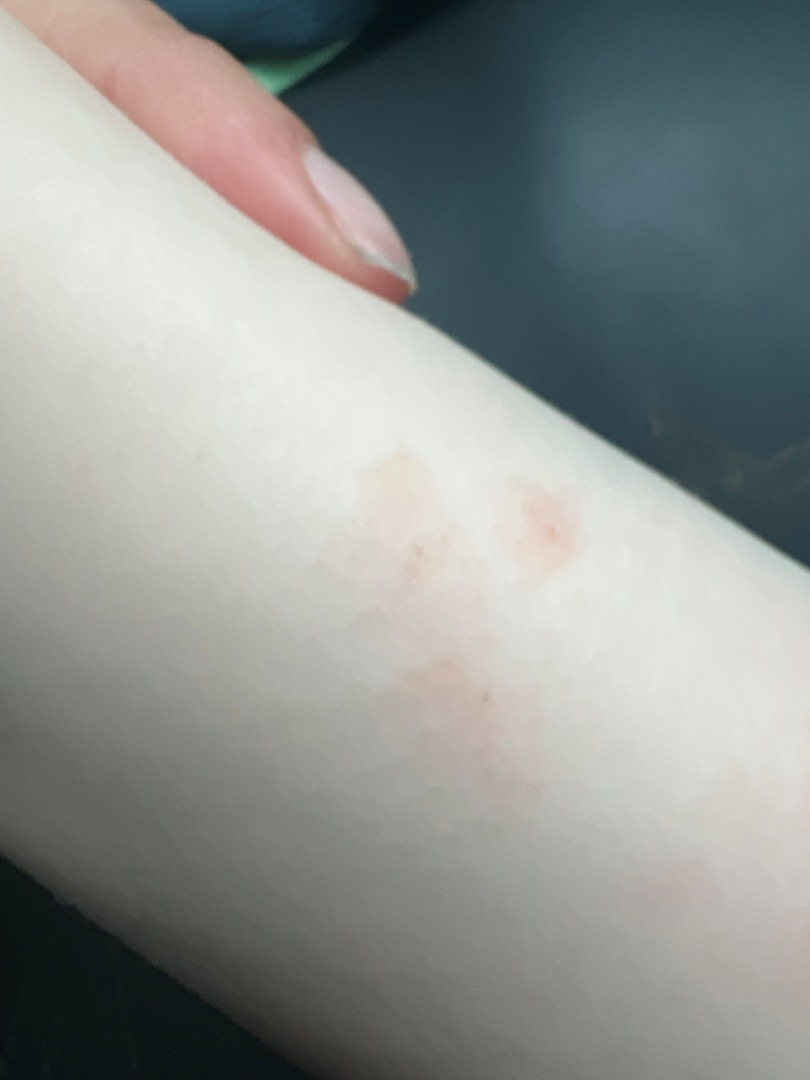The reviewing dermatologist was unable to assign a differential diagnosis from the image.
This image was taken at a distance.